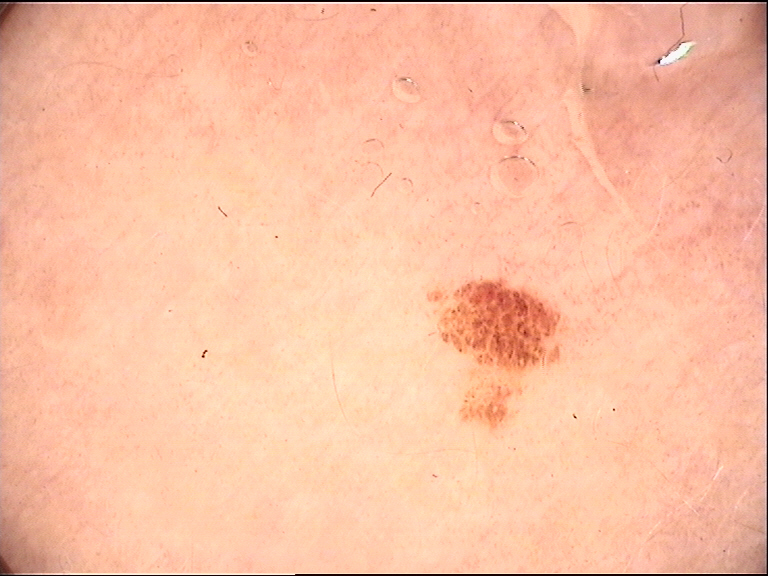A dermoscopy image of a single skin lesion.
Consistent with a banal lesion — a junctional nevus.